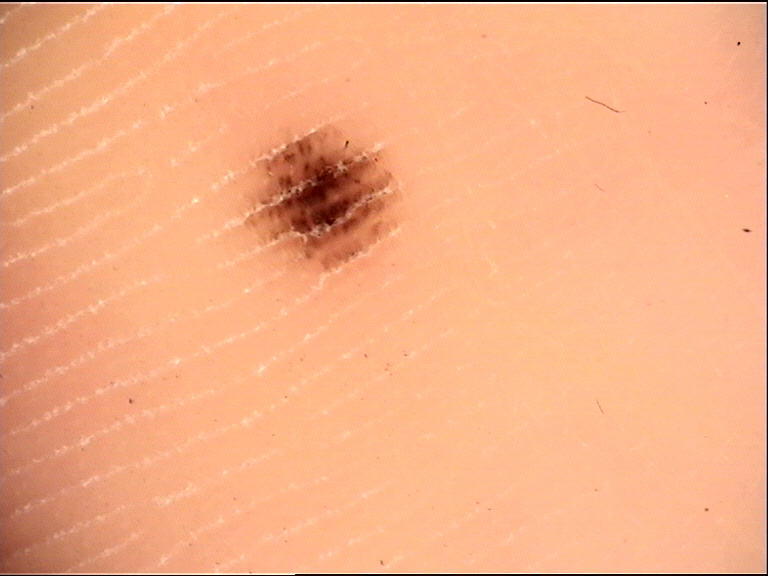Findings: A skin lesion imaged with a dermatoscope. This is a banal lesion. Impression: Classified as an acral junctional nevus.